Female patient, age 18–29. Close-up view. The patient indicates the condition has been present for less than one week. Located on the arm. The patient indicates the lesion is raised or bumpy and fluid-filled:
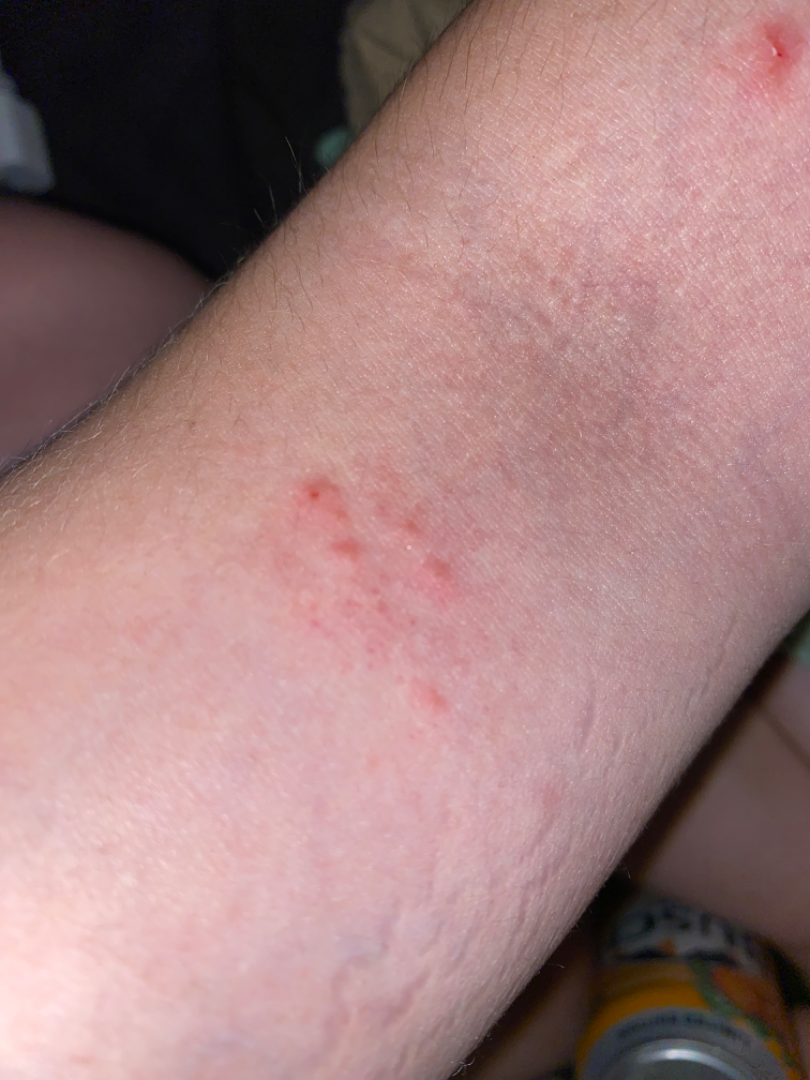On remote review of the image: the differential is split between Allergic Contact Dermatitis; Acute dermatitis, NOS; and Irritant Contact Dermatitis; less likely is Insect Bite; less probable is Eczema.